A close-up photograph — 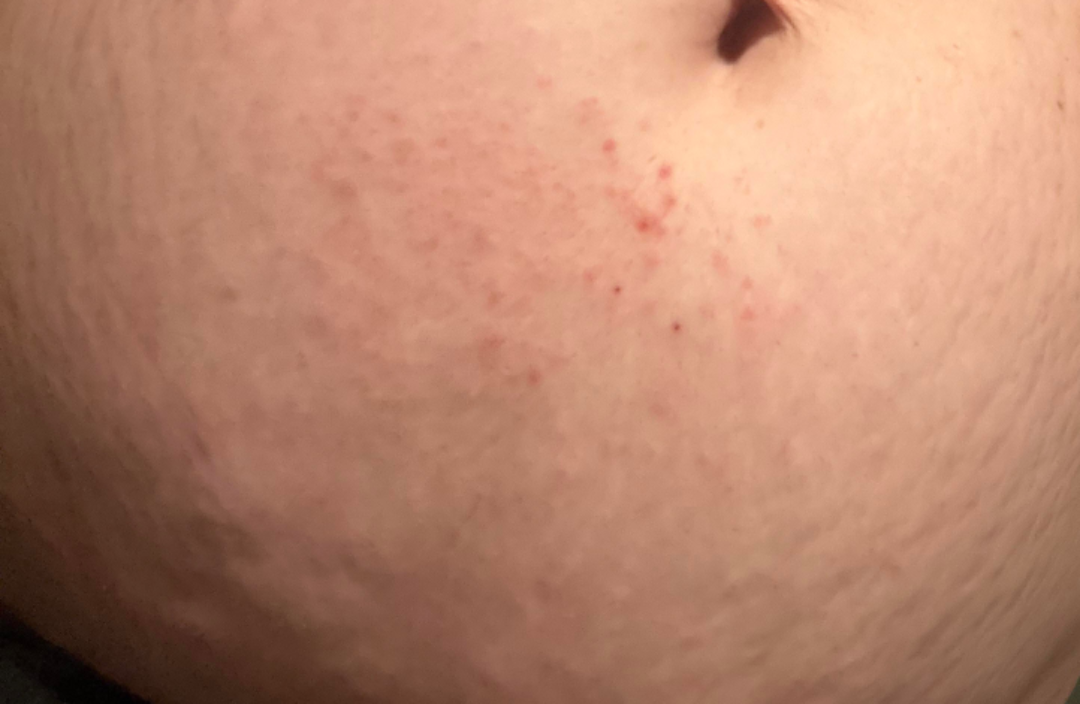Q: What conditions are considered?
A: the favored diagnosis is Eczema; with consideration of Pemphigoid gestationis; possibly Pruritic urticarial papules and plaques of pregnancy